Close-up view; the leg is involved; the contributor is a female aged 18–29:
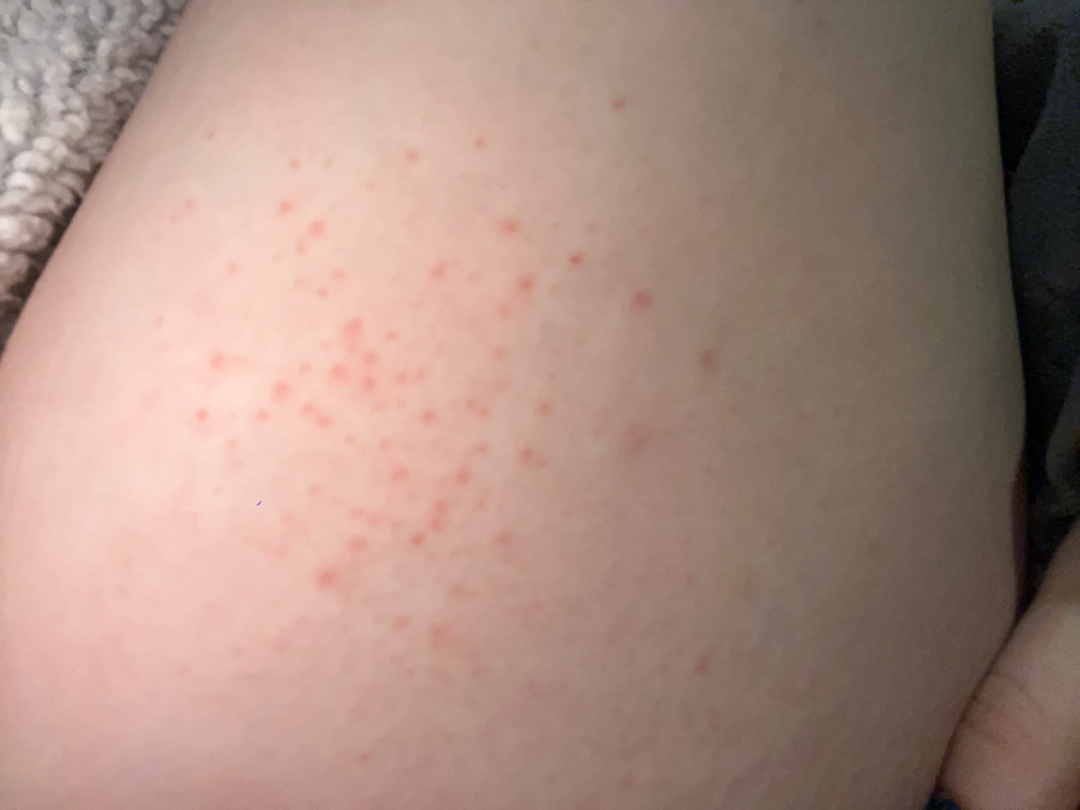{"differential": {"leading": ["Miliaria"], "considered": ["Eczema"]}}